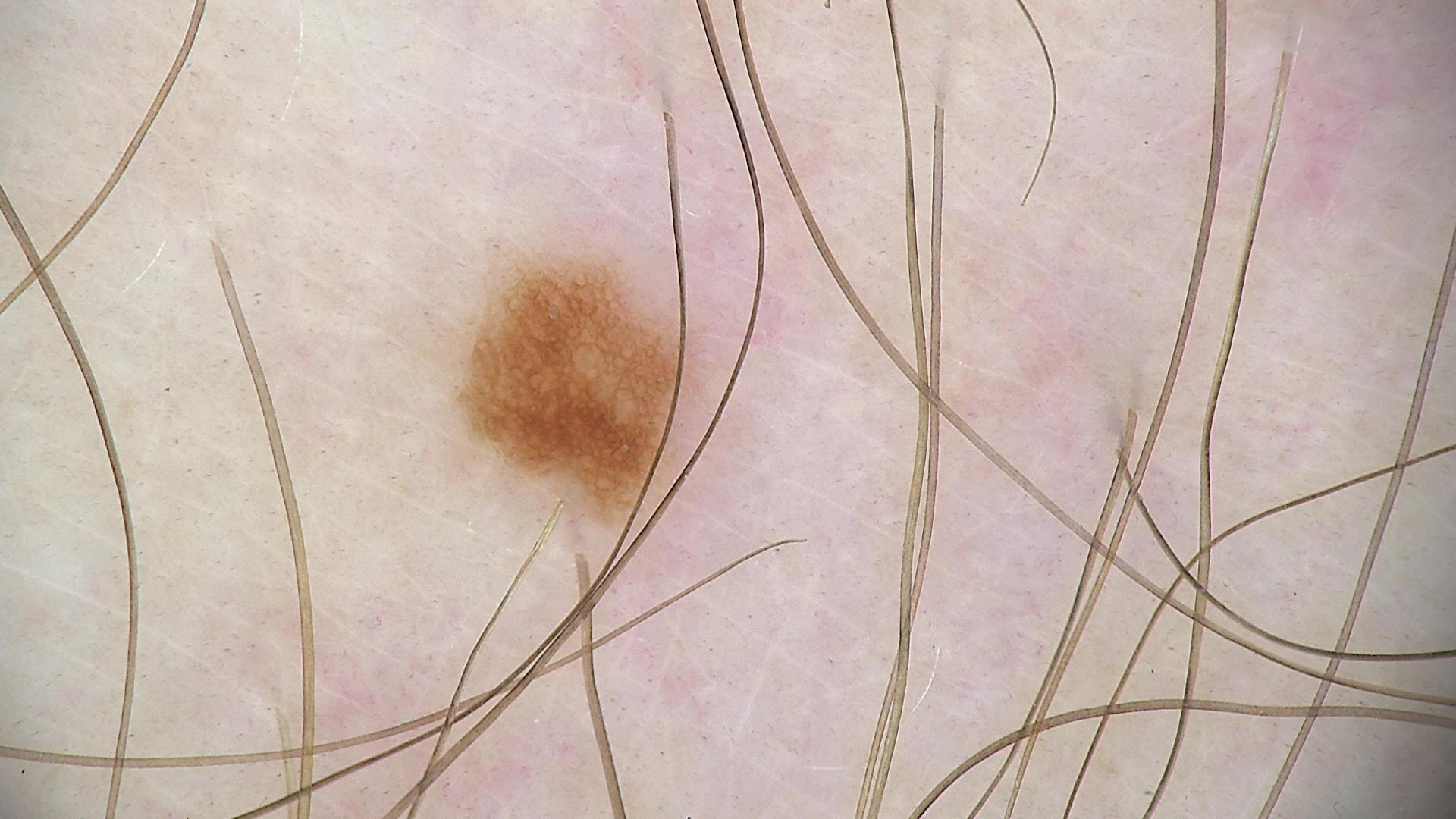Summary: A dermatoscopic image of a skin lesion. Conclusion: Labeled as a benign lesion — a dysplastic junctional nevus.